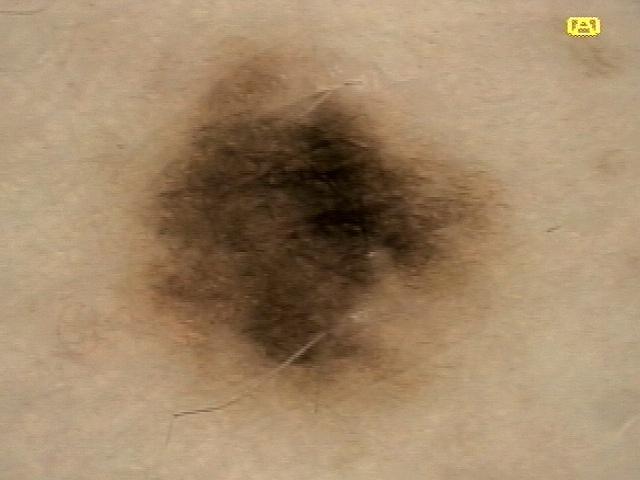Q: Patient demographics?
A: female, aged approximately 40
Q: Where on the body is the lesion?
A: a lower extremity
Q: What did the workup show?
A: Nevus (biopsy-proven)